A clinical close-up photograph of a skin lesion. A patient 57 years of age:
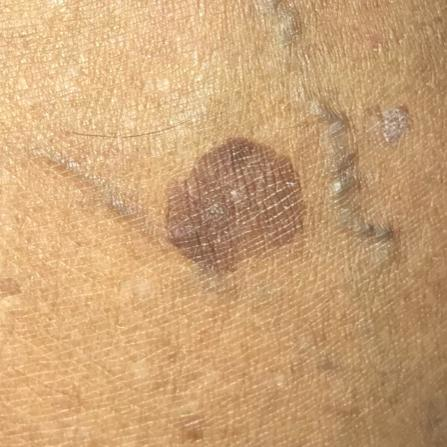<lesion>
  <symptoms>
    <present>growth</present>
  </symptoms>
  <diagnosis>
    <name>seborrheic keratosis</name>
    <code>SEK</code>
    <malignancy>benign</malignancy>
    <confirmation>clinical consensus</confirmation>
  </diagnosis>
</lesion>